A dermoscopic image of a skin lesion:
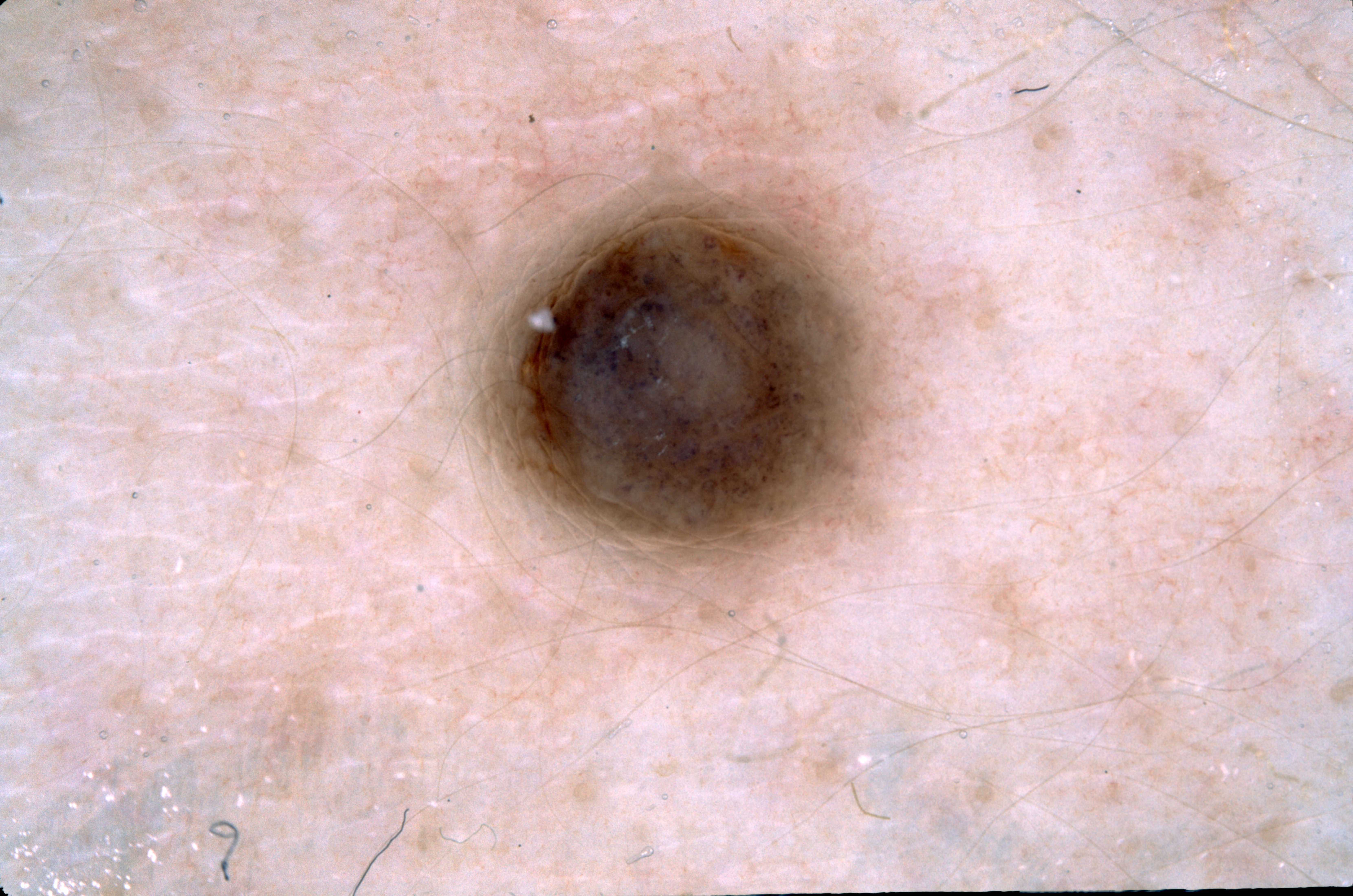• location · bbox(469, 173, 879, 574)
• dermoscopic features assessed but absent · negative network, streaks, pigment network, and milia-like cysts
• impression · a melanocytic nevus